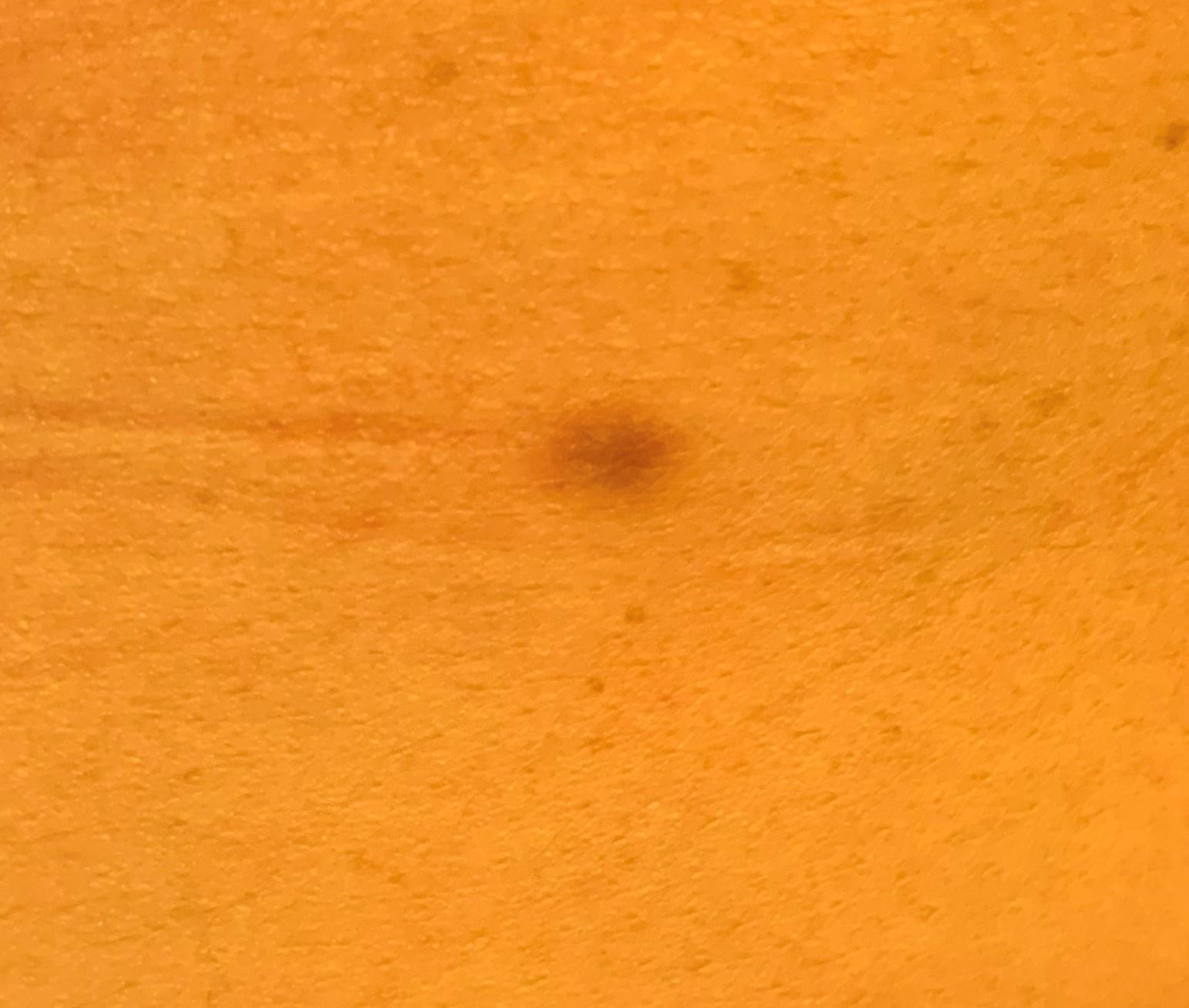{"patient": {"age_approx": 45, "sex": "female"}, "image": "clinical photo (overview)", "lesion_location": {"region": "the trunk", "detail": "the anterior trunk"}, "diagnosis": {"name": "Dermatofibroma", "malignancy": "benign", "confirmation": "expert clinical impression", "lineage": "fibro-histiocytic"}}